A dermoscopic image of a skin lesion:
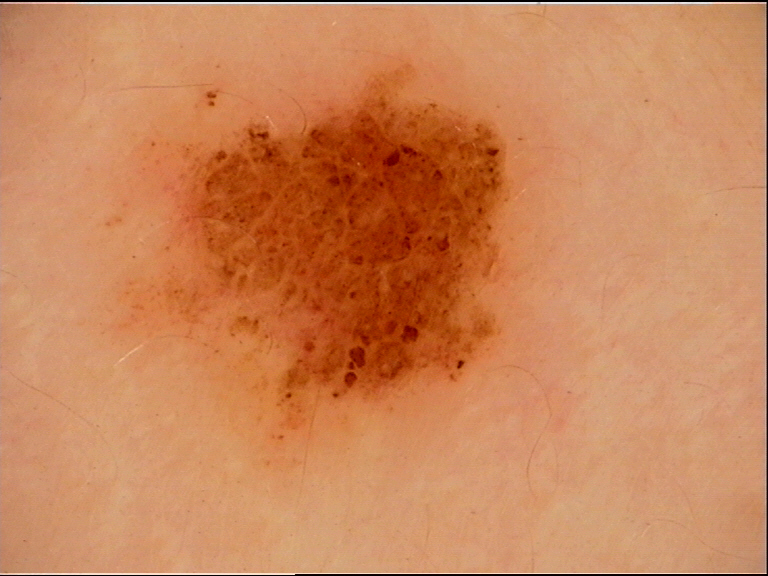Consistent with a dysplastic compound nevus.